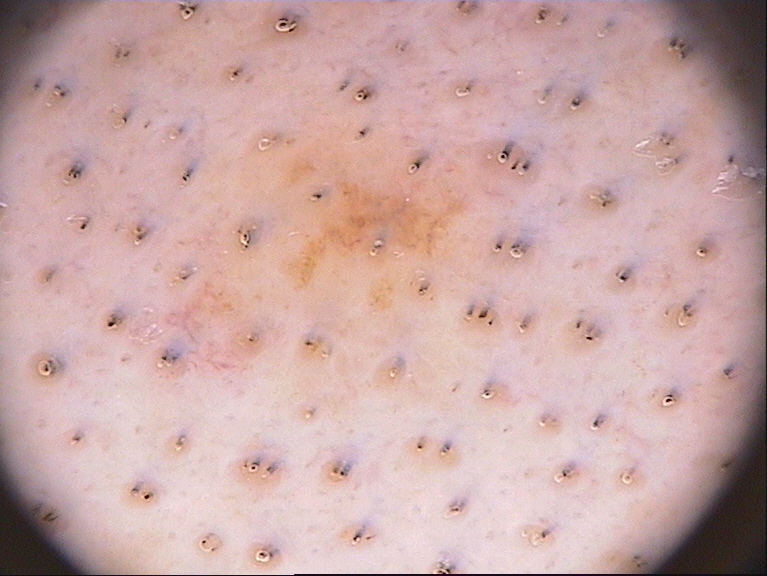Q: What are the patient's age and sex?
A: male, aged 38-42
Q: How was this image acquired?
A: dermoscopy
Q: What does dermoscopy show?
A: globules; absent: pigment network, streaks, negative network, and milia-like cysts
Q: Where is the lesion located?
A: left=239, top=121, right=469, bottom=344
Q: How much of the field does the lesion occupy?
A: ~8% of the field
Q: What did the assessment conclude?
A: a melanocytic nevus, a benign lesion